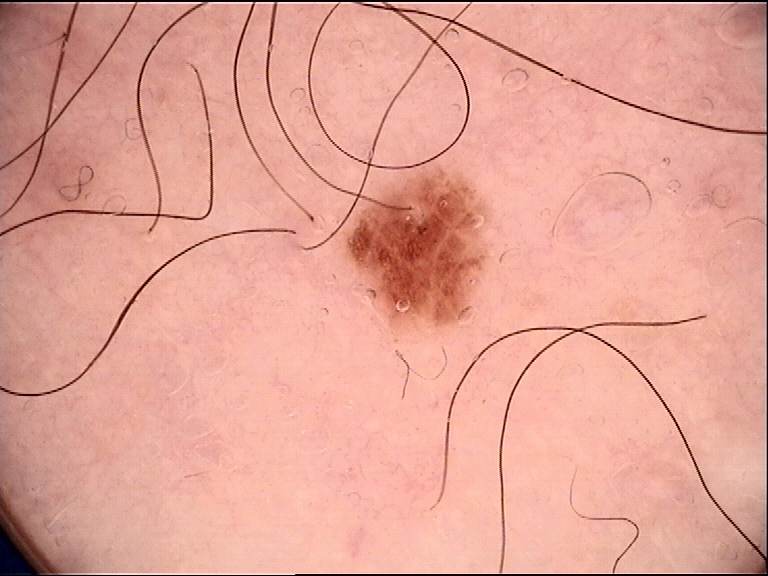{"image": "dermoscopy", "diagnosis": {"name": "dysplastic junctional nevus", "code": "jd", "malignancy": "benign", "super_class": "melanocytic", "confirmation": "expert consensus"}}